The subject is a female aged 18–29. A close-up photograph. The lesion involves the palm and top or side of the foot.
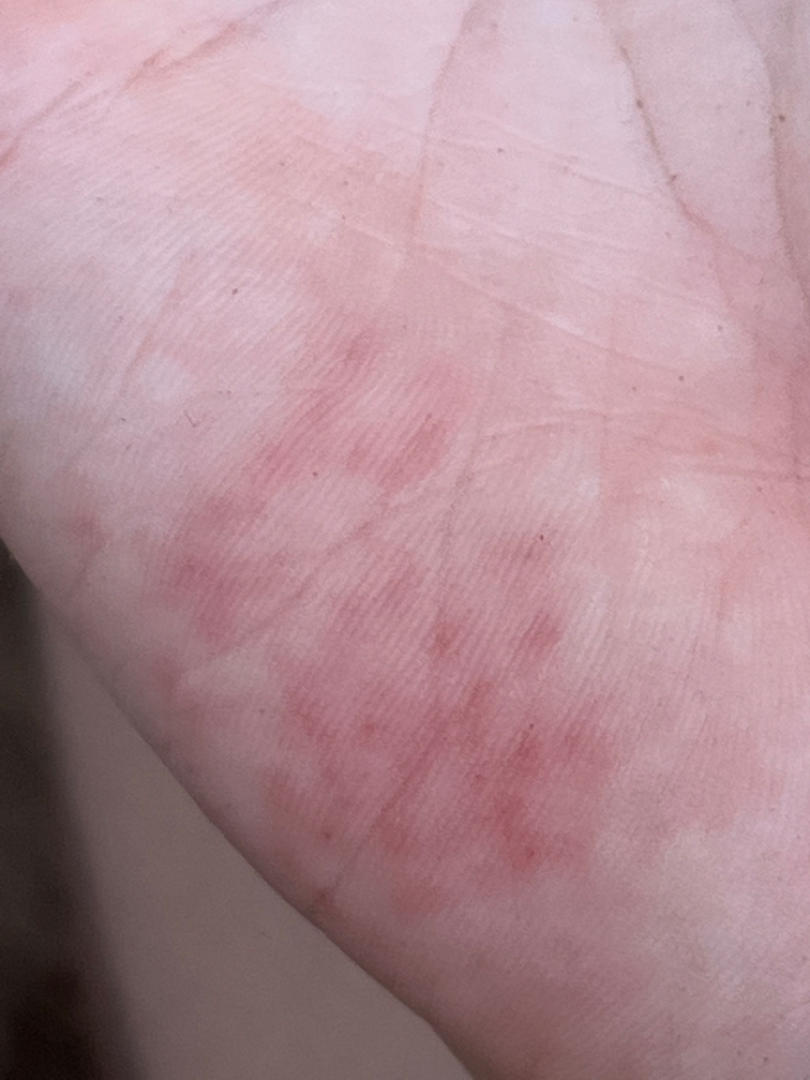Q: What was the assessment?
A: indeterminate